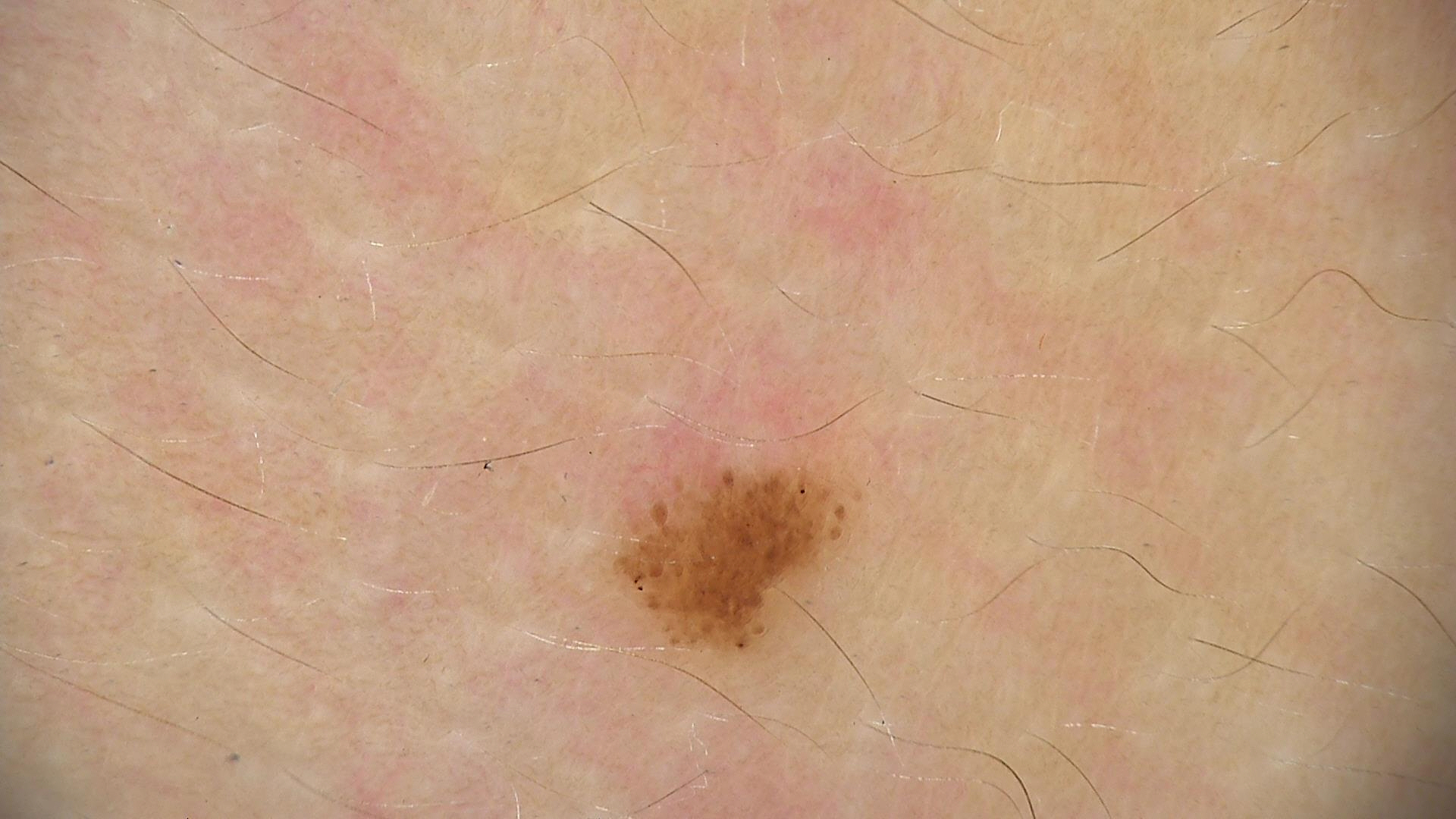The diagnosis was a dysplastic junctional nevus.